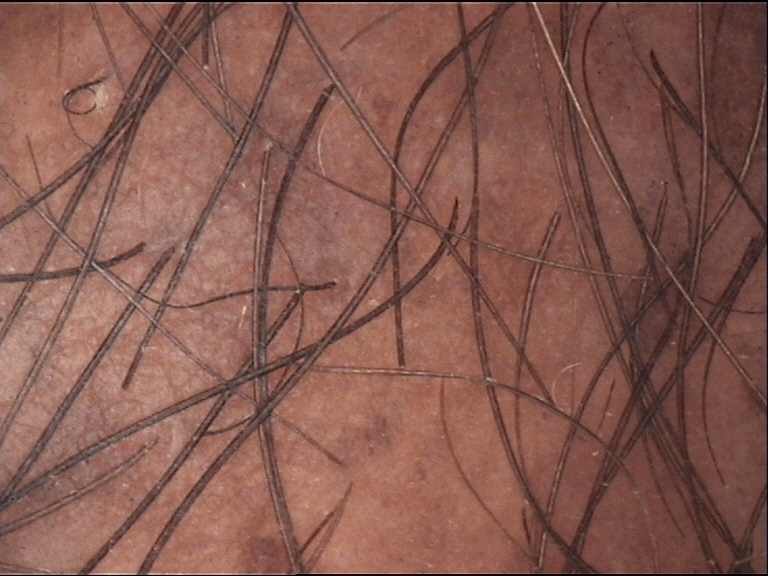This is a banal lesion.
Labeled as a congenital compound nevus.